The patient is a female aged approximately 45; a skin lesion imaged with a dermatoscope.
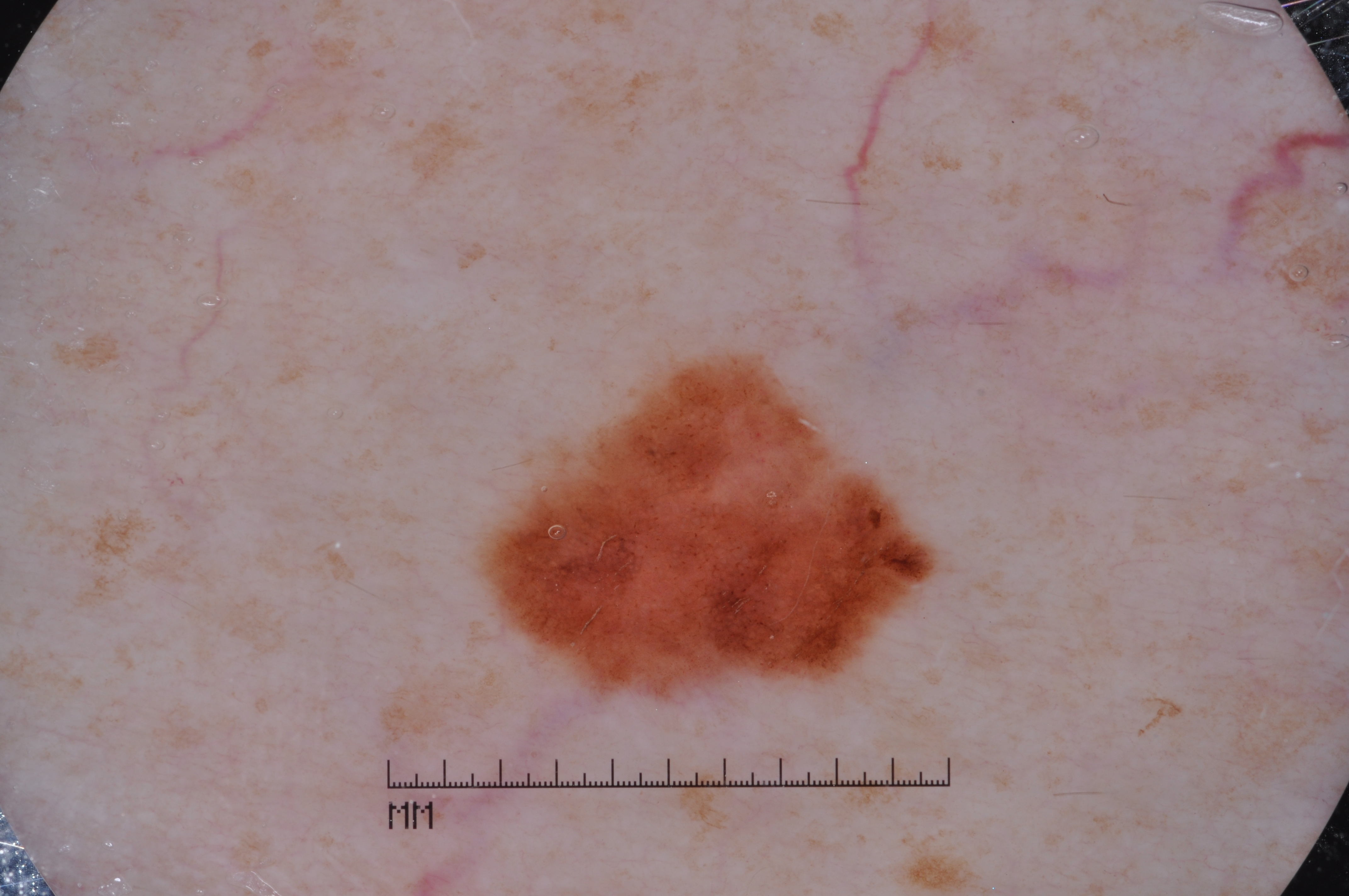Notes:
* bounding box — <box>485, 357, 927, 693</box>
* features — pigment network; absent: streaks, negative network, and milia-like cysts
* extent — ~8% of the field
* impression — a melanoma, a malignant skin lesion